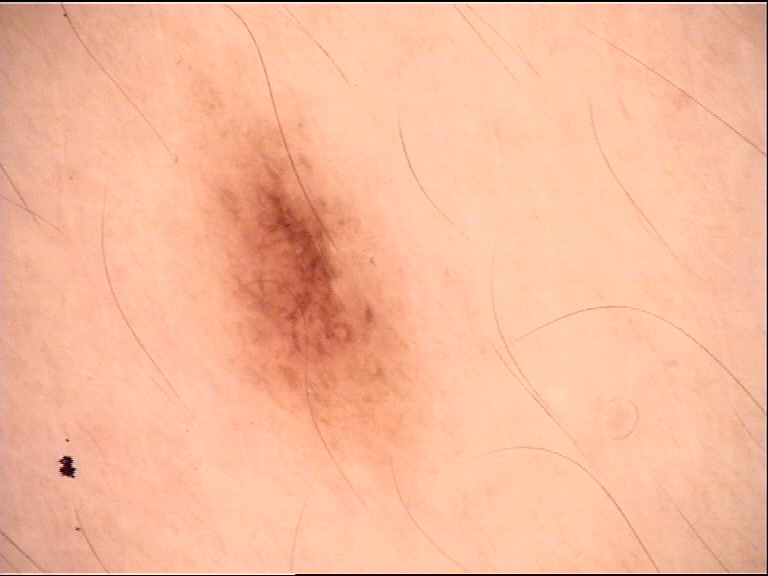Dermoscopy of a skin lesion. Labeled as a banal lesion — a junctional nevus.